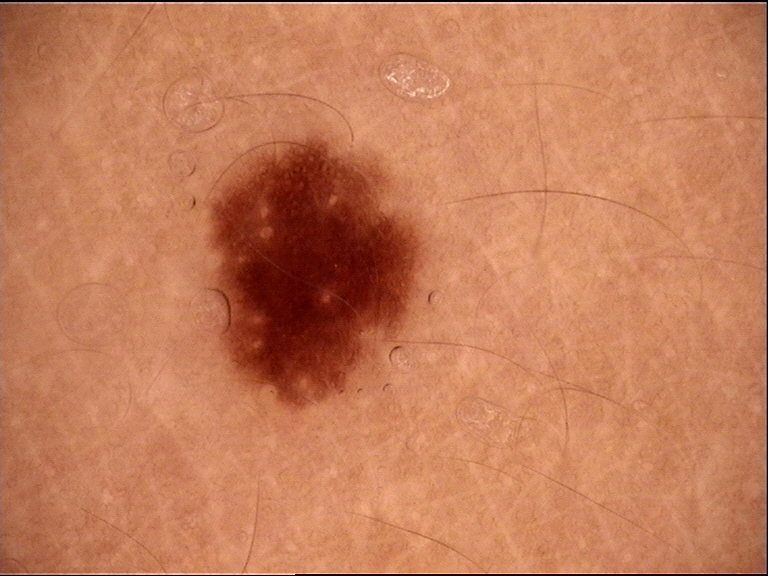Classified as a dysplastic junctional nevus.